A clinical photo of a skin lesion taken with a smartphone.
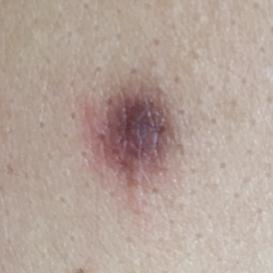Summary: The lesion is on the back. The patient describes that the lesion is elevated, but does not itch. Conclusion: The consensus clinical diagnosis was a benign skin lesion — a nevus.